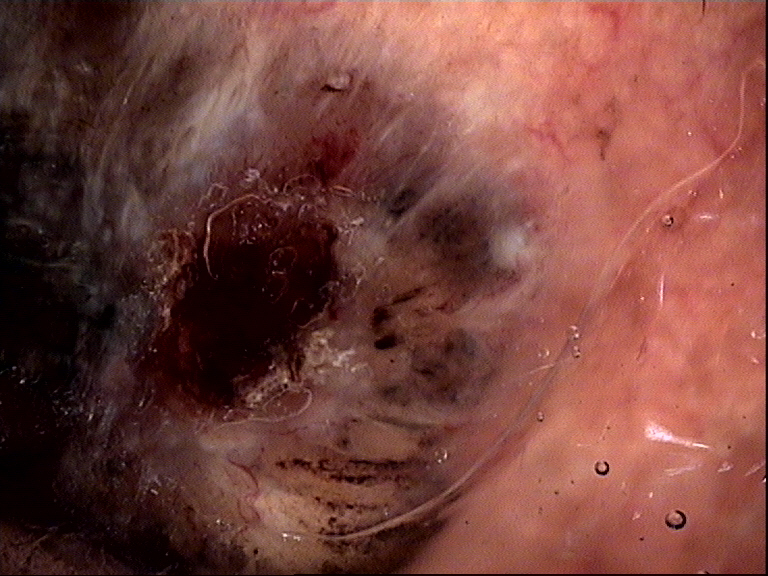modality=dermoscopy; class=basal cell carcinoma (biopsy-proven).